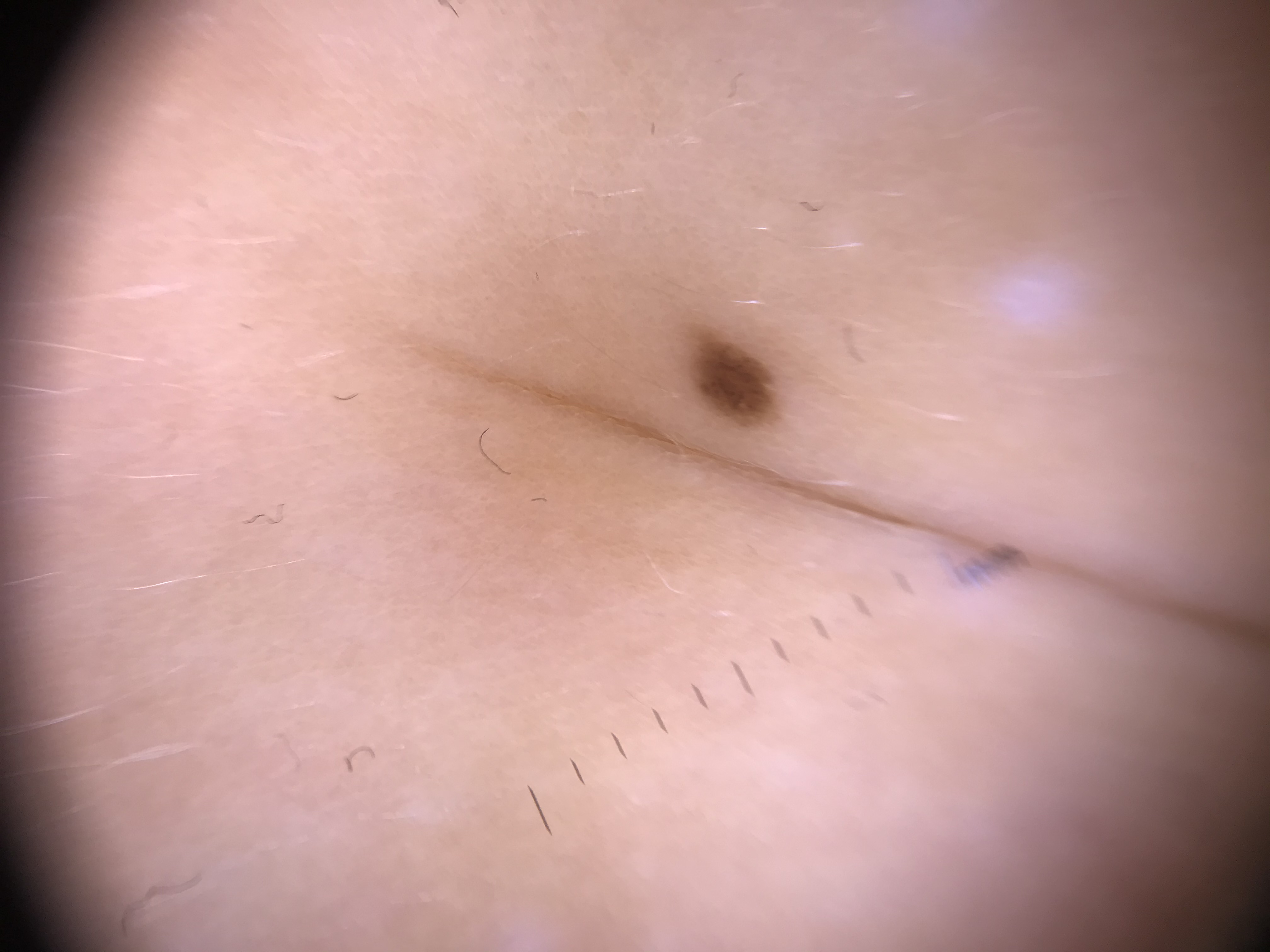Labeled as a junctional nevus.